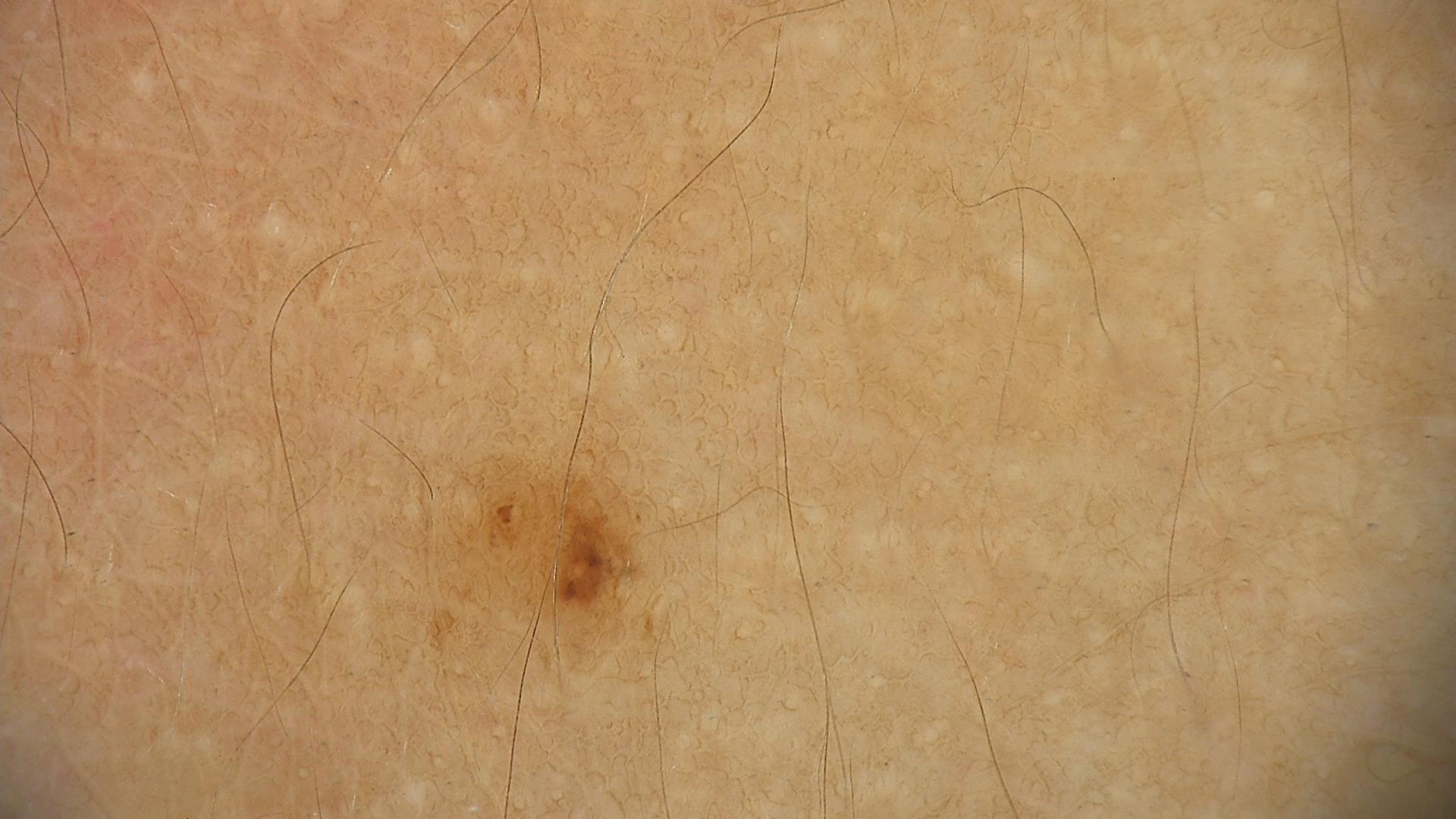A dermatoscopic image of a skin lesion. Consistent with a dysplastic junctional nevus.